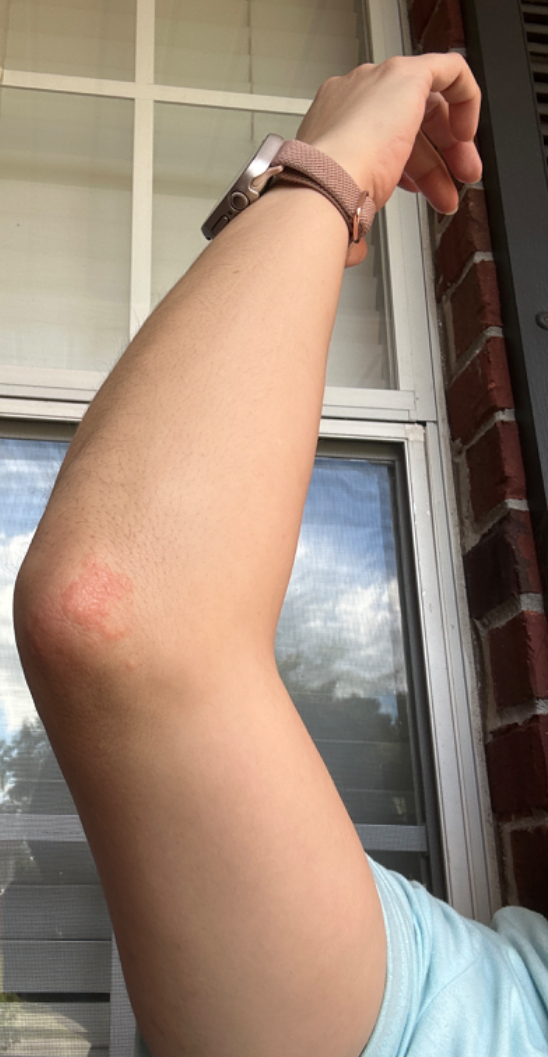Case summary:
* assessment — unable to determine